This image was taken at a distance · the condition has been present for one to four weeks · the patient indicates the lesion is raised or bumpy, fluid-filled and rough or flaky · located on the arm, back of the hand, head or neck and leg:
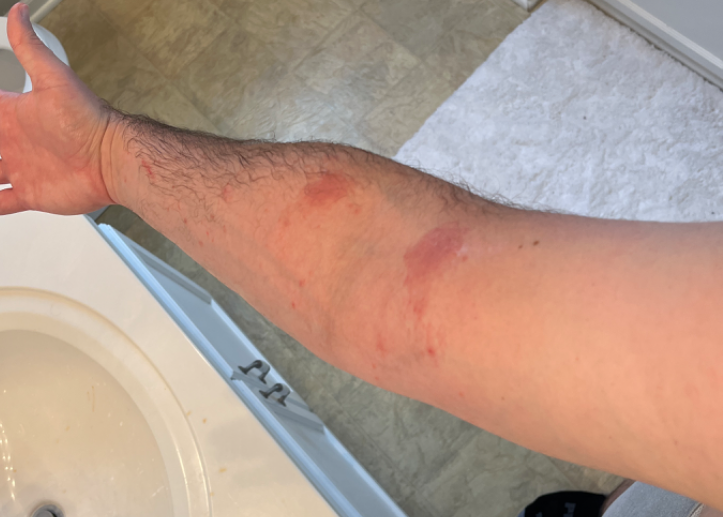Allergic Contact Dermatitis (leading); Irritant Contact Dermatitis (possible); Urticaria (less likely).